Recorded as FST II · a male subject in their 50s · by history, prior malignancy (patient or family), alcohol use, no prior skin cancer (patient or family), and no tobacco use · a clinical close-up photograph of a skin lesion: 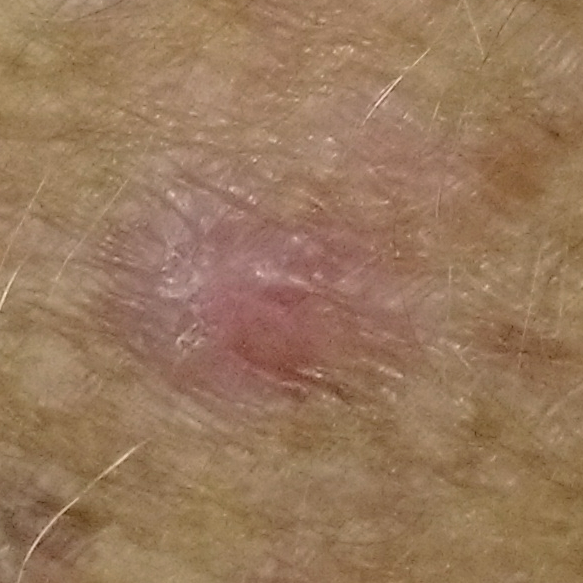The patient describes that the lesion is elevated. Histopathologically confirmed as a basal cell carcinoma.